A dermatoscopic image of a skin lesion: 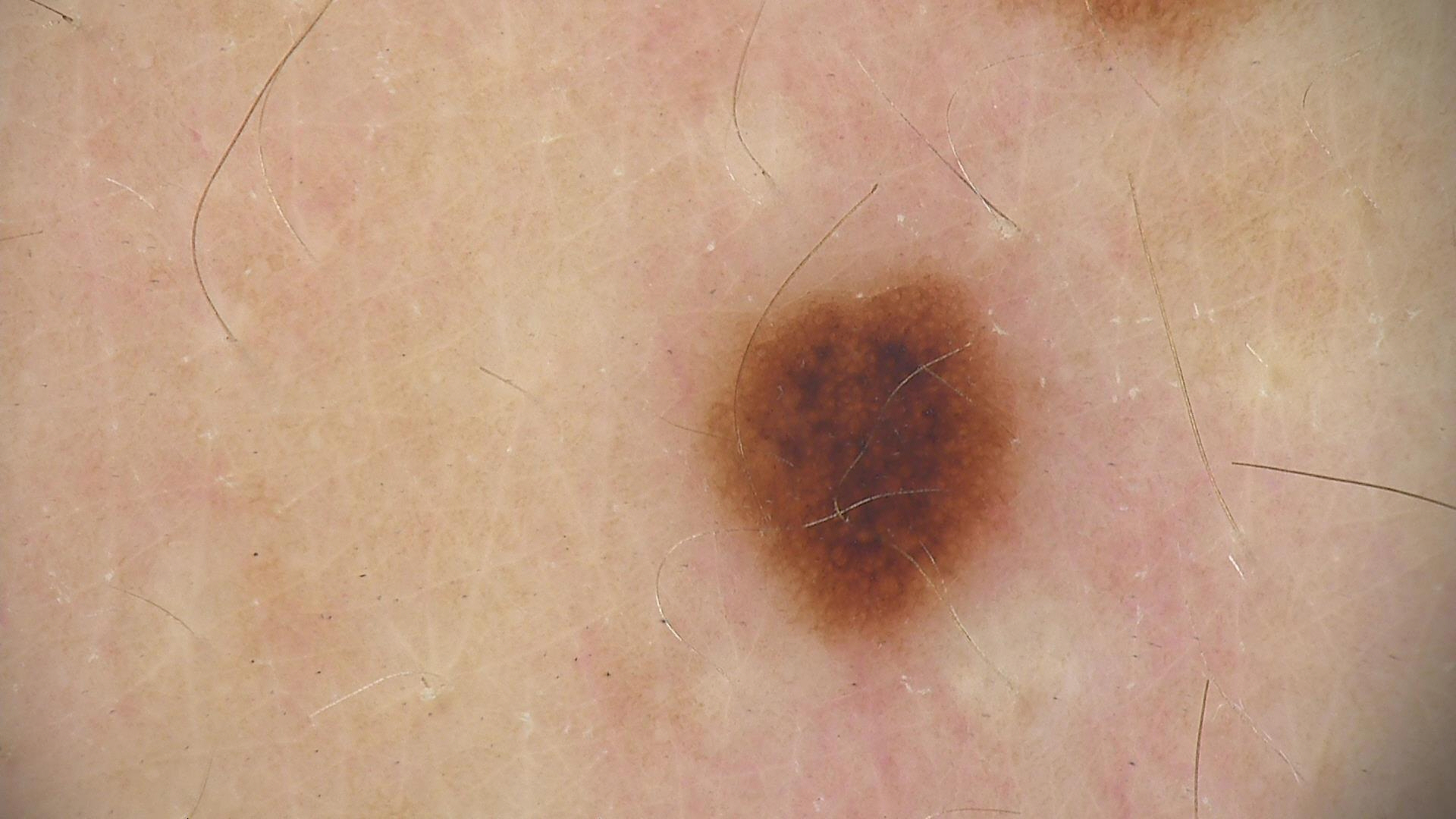diagnosis:
  name: dysplastic junctional nevus
  code: jd
  malignancy: benign
  super_class: melanocytic
  confirmation: expert consensus